A subject age 75 · a clinical close-up photograph of a skin lesion.
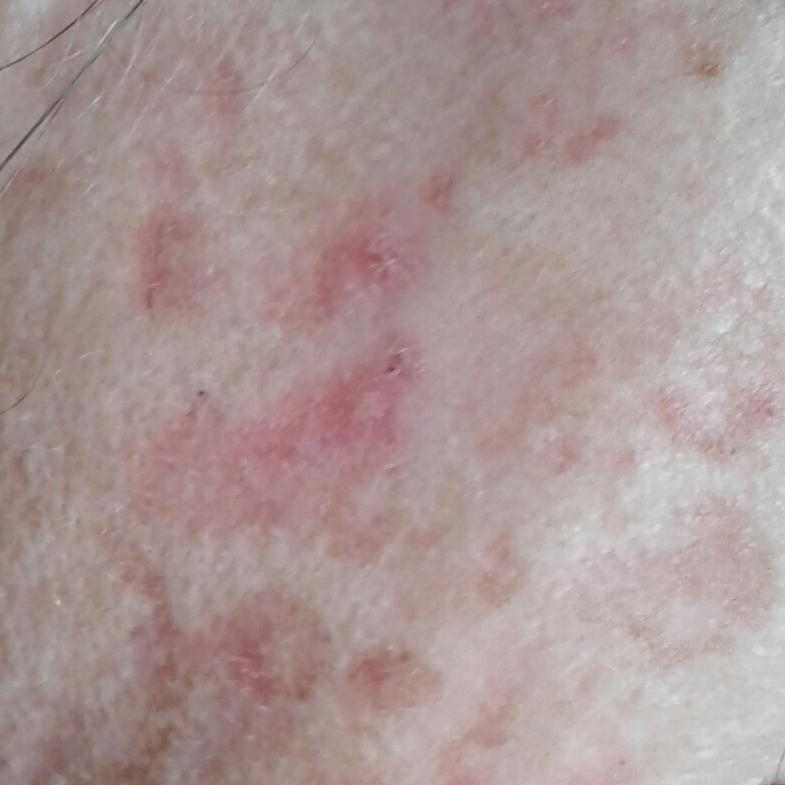Clinical context: Located on the face. The patient describes that the lesion itches, but does not hurt. Conclusion: Diagnosed by dermatologist consensus as an actinic keratosis.